A dermoscopic close-up of a skin lesion. A male subject, aged 68-72.
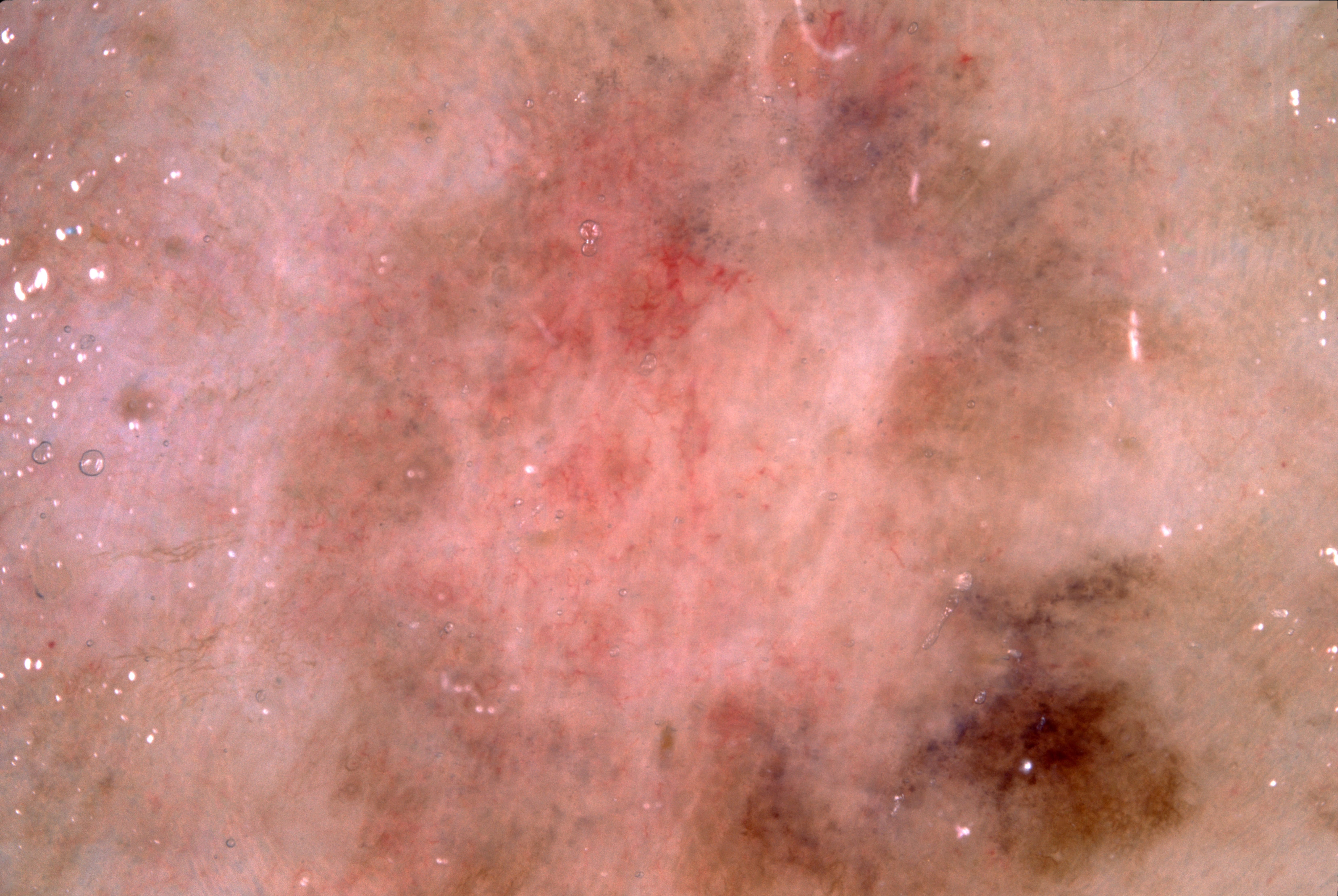As (left, top, right, bottom), the lesion spans bbox(219, 0, 1275, 895). Dermoscopically, the lesion shows pigment network and negative network. Histopathologically confirmed as a melanoma, a malignancy.